A close-up photograph; the affected area is the front of the torso, back of the torso, leg and arm — 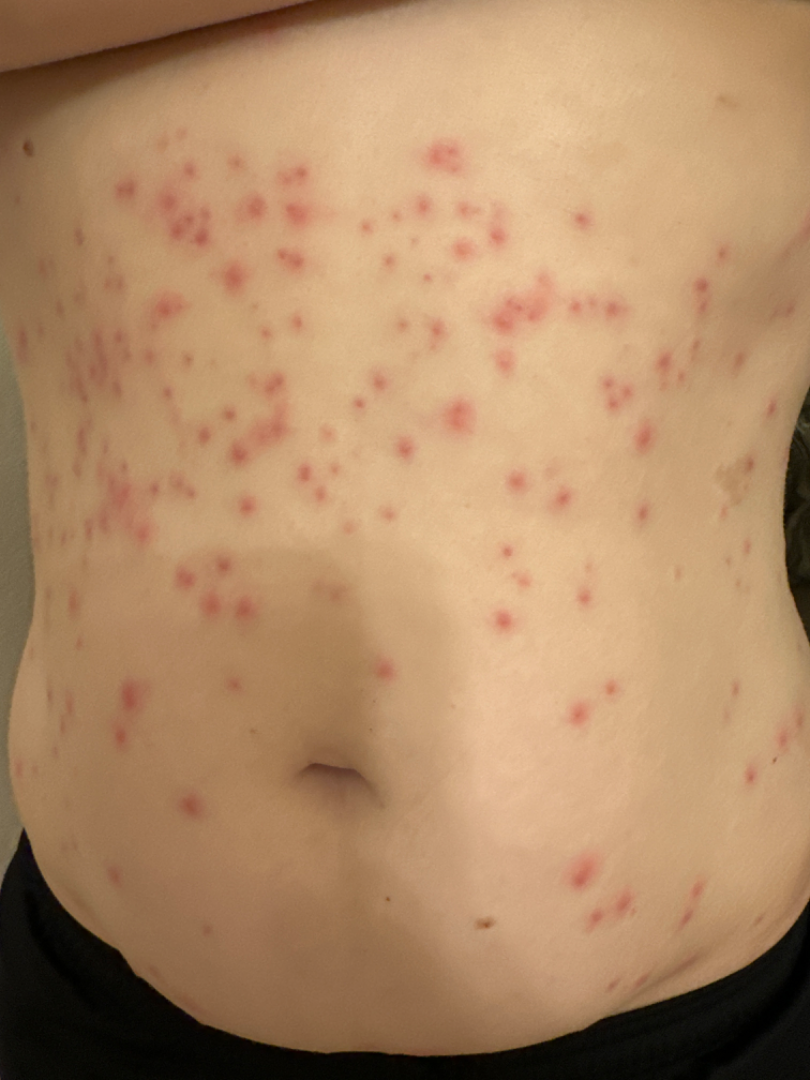reported symptoms = itching and bothersome appearance
onset = less than one week
described texture = raised or bumpy
associated systemic symptoms = none reported
clinical impression = three independent reviewers: favoring Insect Bite; lower on the differential is Drug Rash; less likely is Chicken pox exanthem; a more distant consideration is Pityriasis lichenoides; less probable is Scabies; a remote consideration is Infected eczema